Located on the back of the hand, arm and leg · the subject is a female aged 50–59 · the photo was captured at an angle.
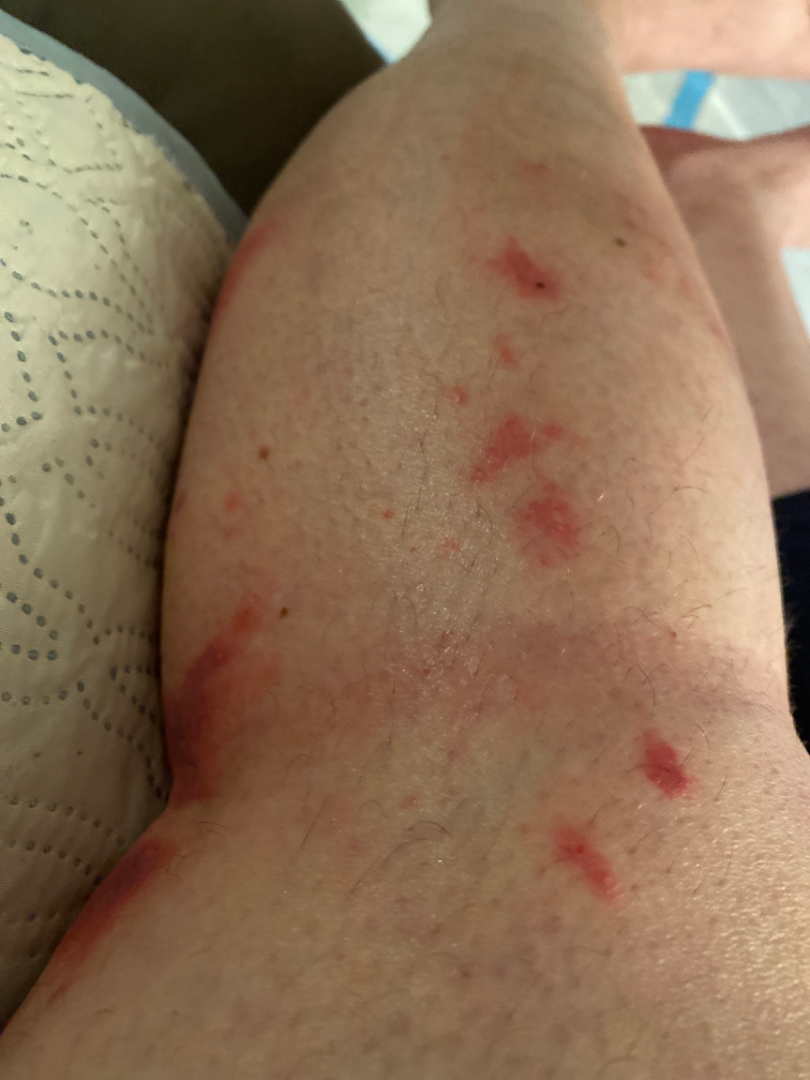assessment = could not be assessed.